Present for three to twelve months, the patient reported no relevant symptoms from the lesion, the patient described the issue as a nail problem, the lesion involves the palm and back of the hand, the lesion is described as rough or flaky, an image taken at an angle — 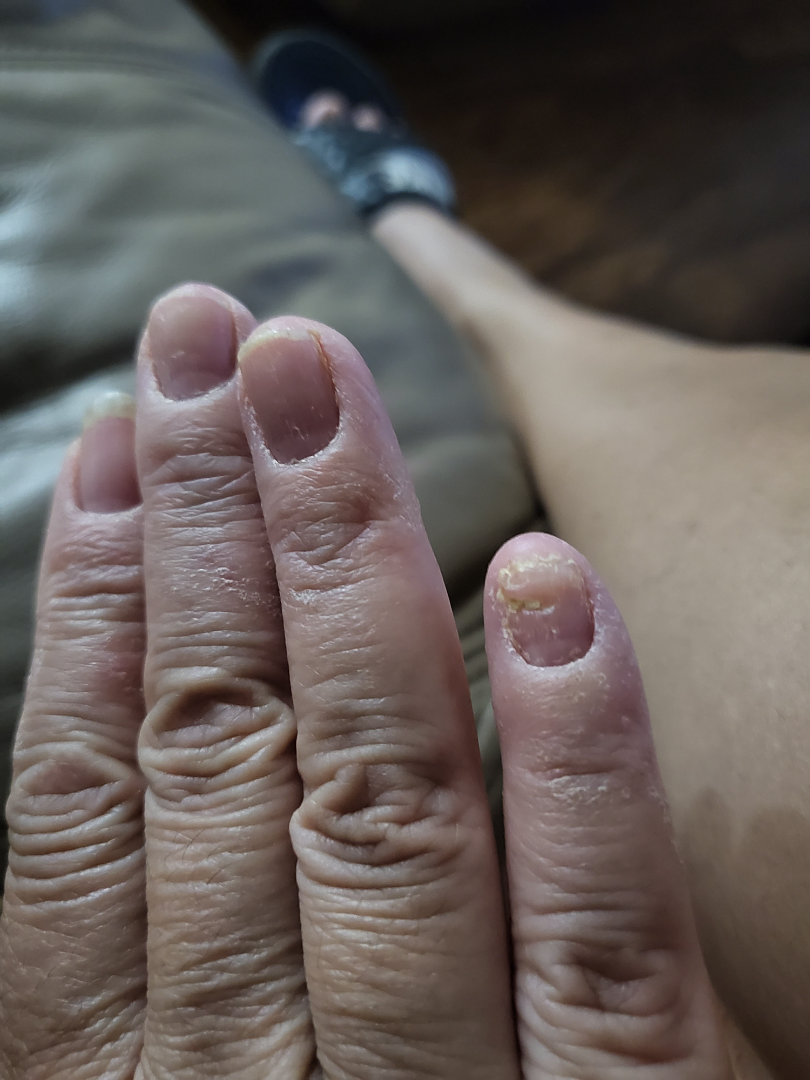{
  "assessment": "no findings on review"
}